The patient considered this a rash, symptoms reported: itching, no constitutional symptoms were reported, the lesion is described as raised or bumpy, the photograph was taken at a distance, present for about one day, the arm is involved — 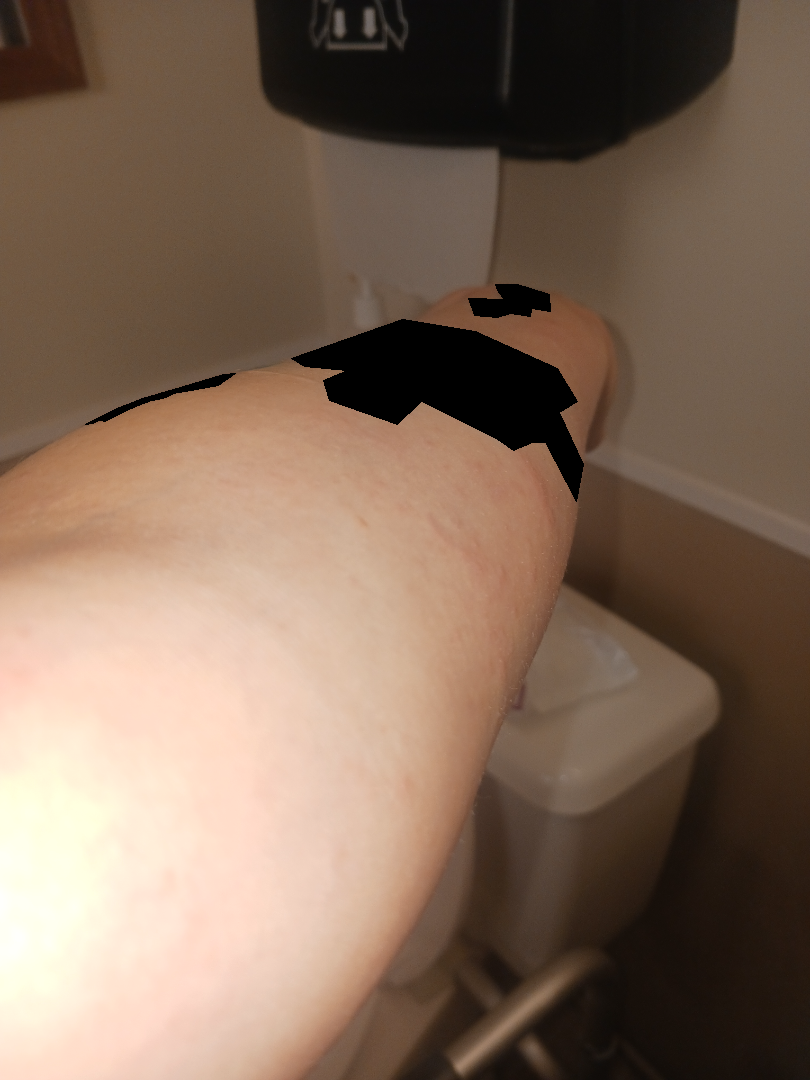The dermatologist could not determine a likely condition from the photograph alone.